Dermoscopy of a skin lesion: 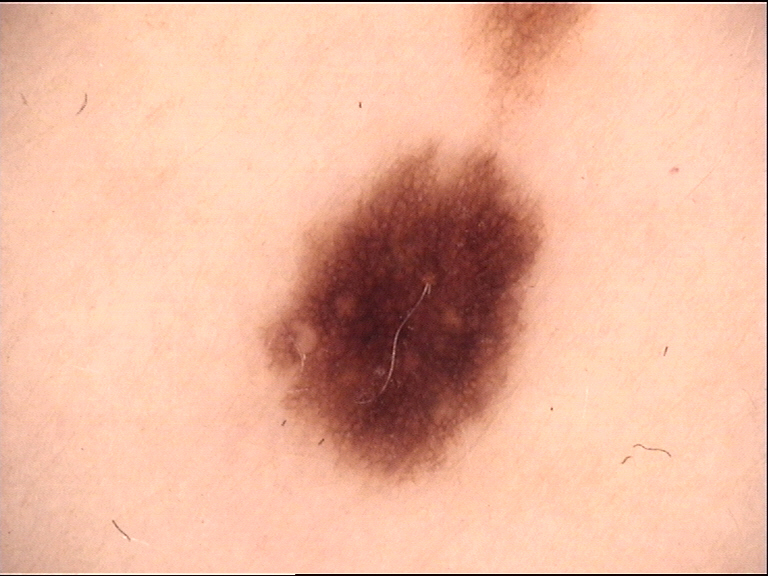Classified as a benign lesion — a dysplastic junctional nevus.